A skin lesion imaged with a dermatoscope — 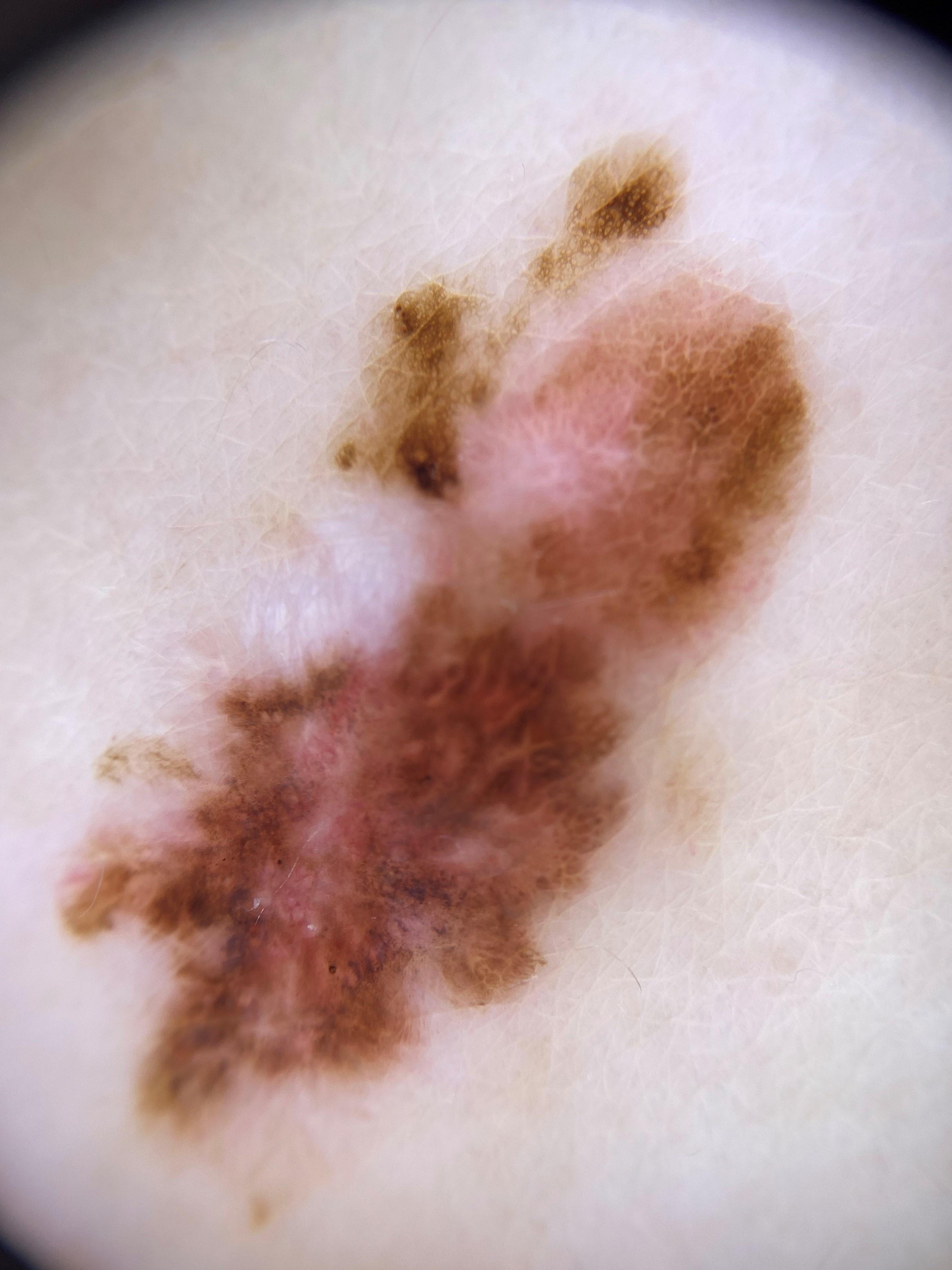lesion_location:
  region: the trunk
  detail: the anterior trunk
diagnosis:
  name: Melanoma
  malignancy: malignant
  confirmation: histopathology